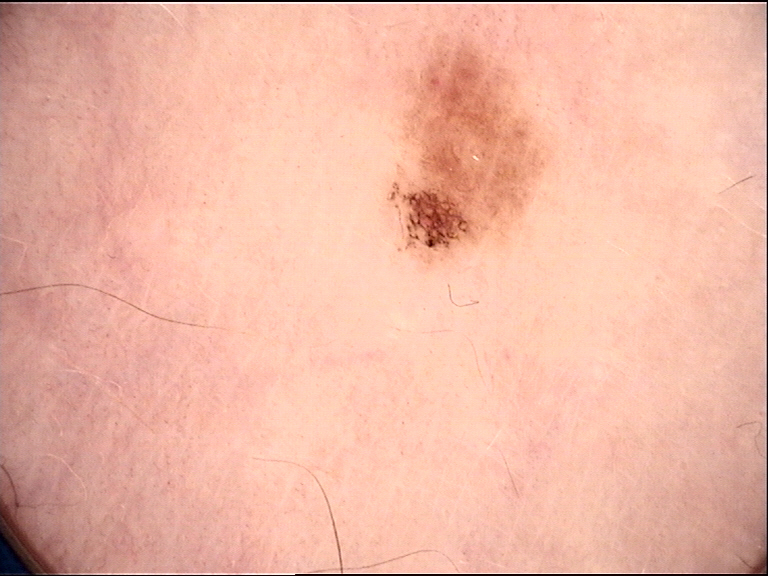Q: What was the diagnostic impression?
A: dysplastic junctional nevus (expert consensus)